Dermoscopy of a skin lesion: 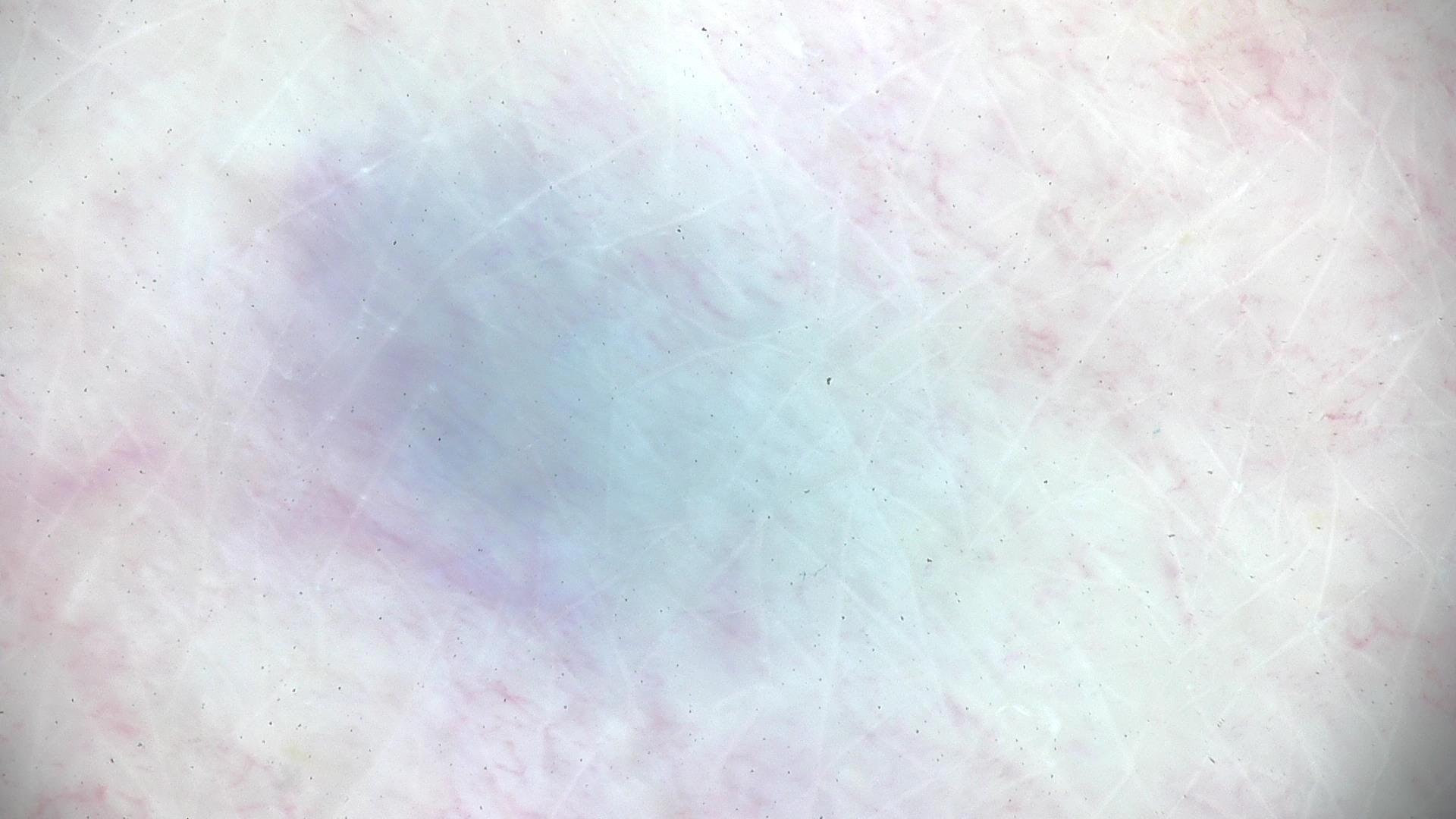category=dermal, banal; label=blue nevus (expert consensus).